Dermoscopy of a skin lesion.
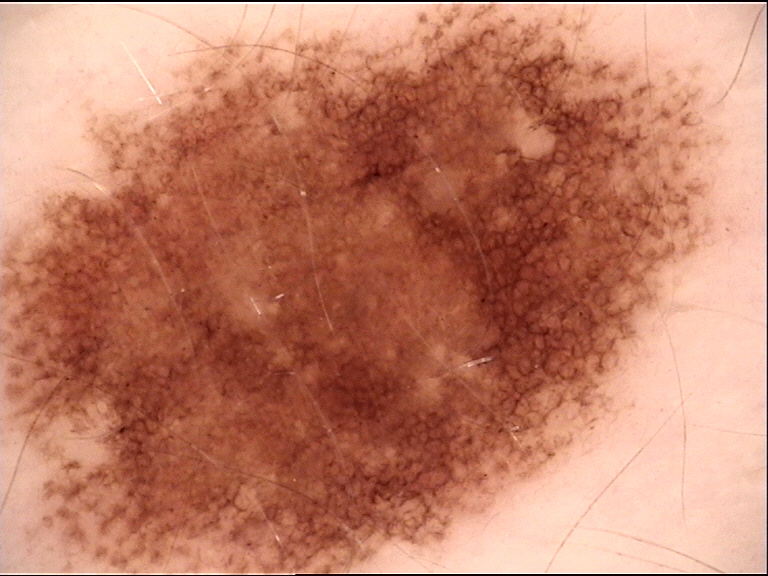label: dysplastic junctional nevus (expert consensus).